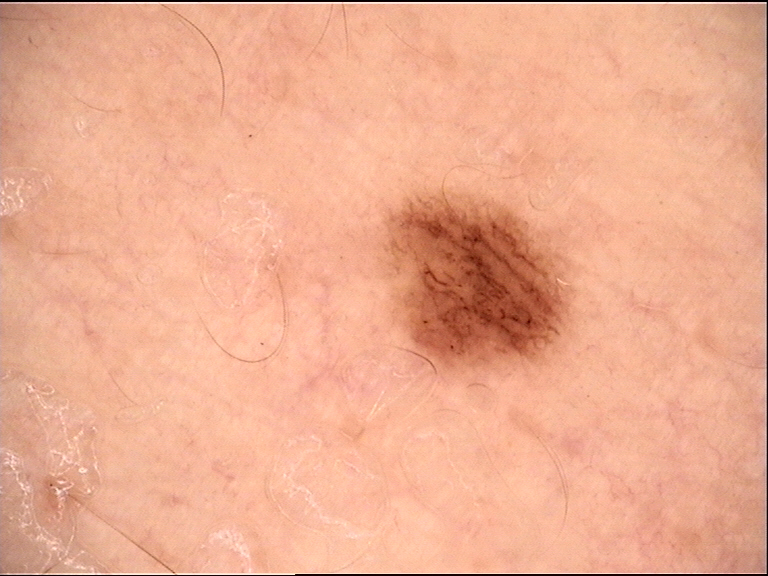| feature | finding |
|---|---|
| image type | dermoscopy |
| diagnosis | dysplastic junctional nevus (expert consensus) |